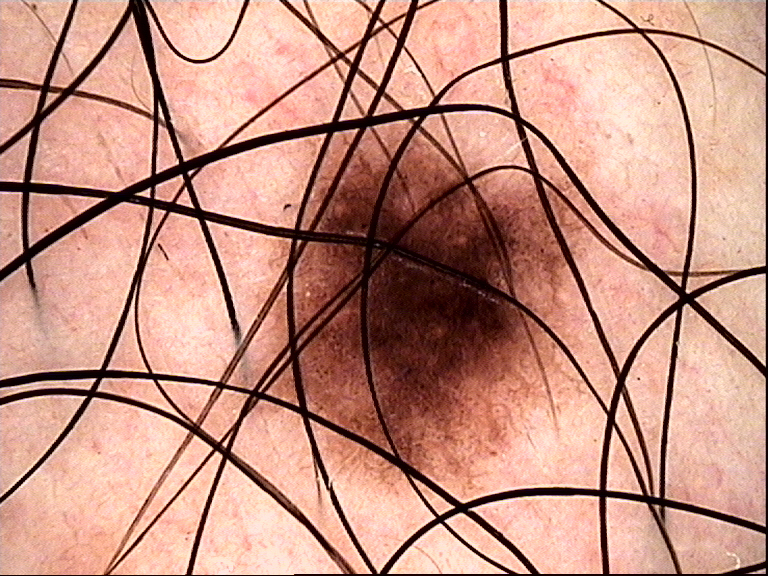A skin lesion imaged with a dermatoscope. The diagnosis was a benign lesion — a dysplastic junctional nevus.